Dermoscopy of a skin lesion. Acquired for a research image collection, with no referral diagnosis — 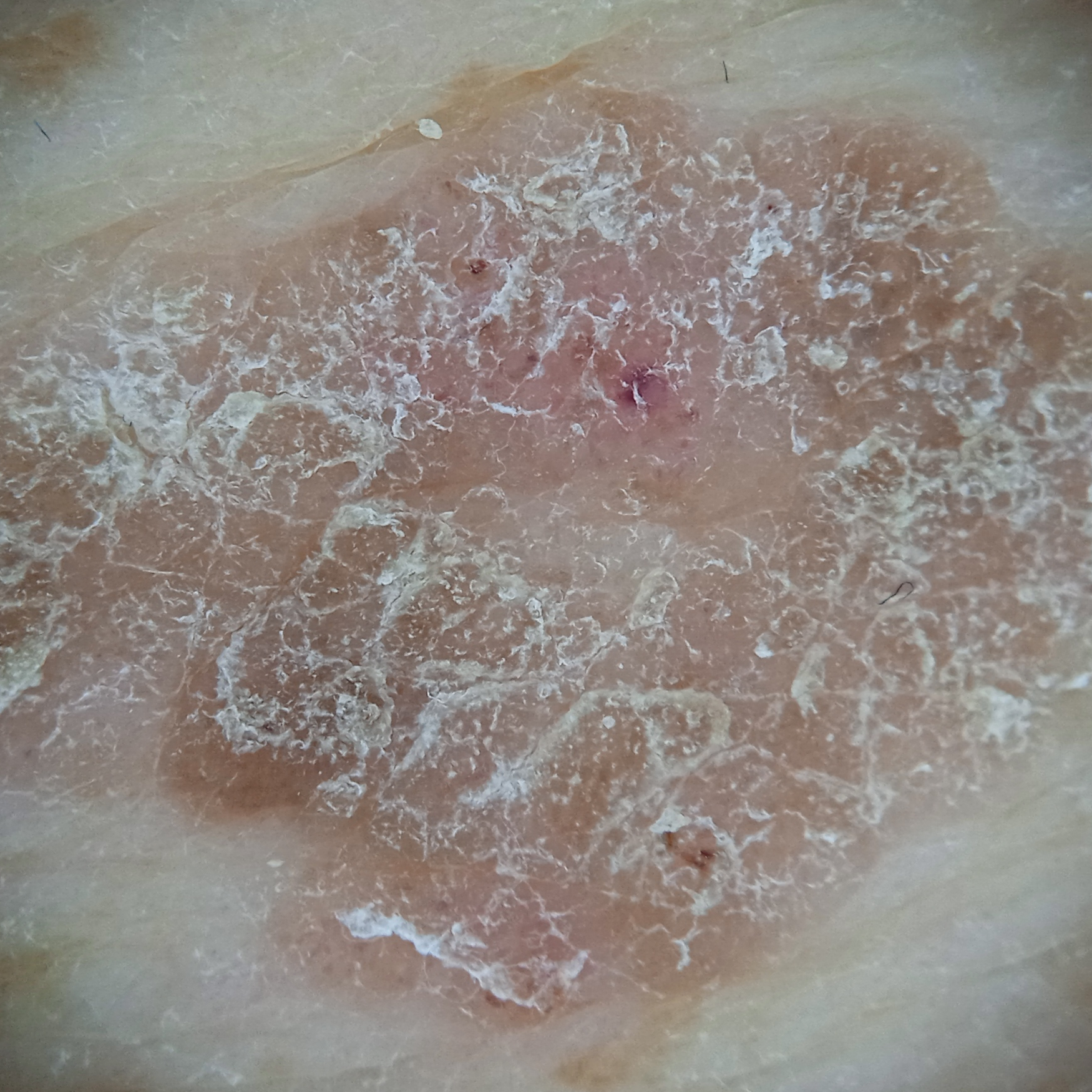The lesion involves the back. The lesion measures approximately 16.5 mm. The consensus diagnosis for this lesion was a seborrheic keratosis.